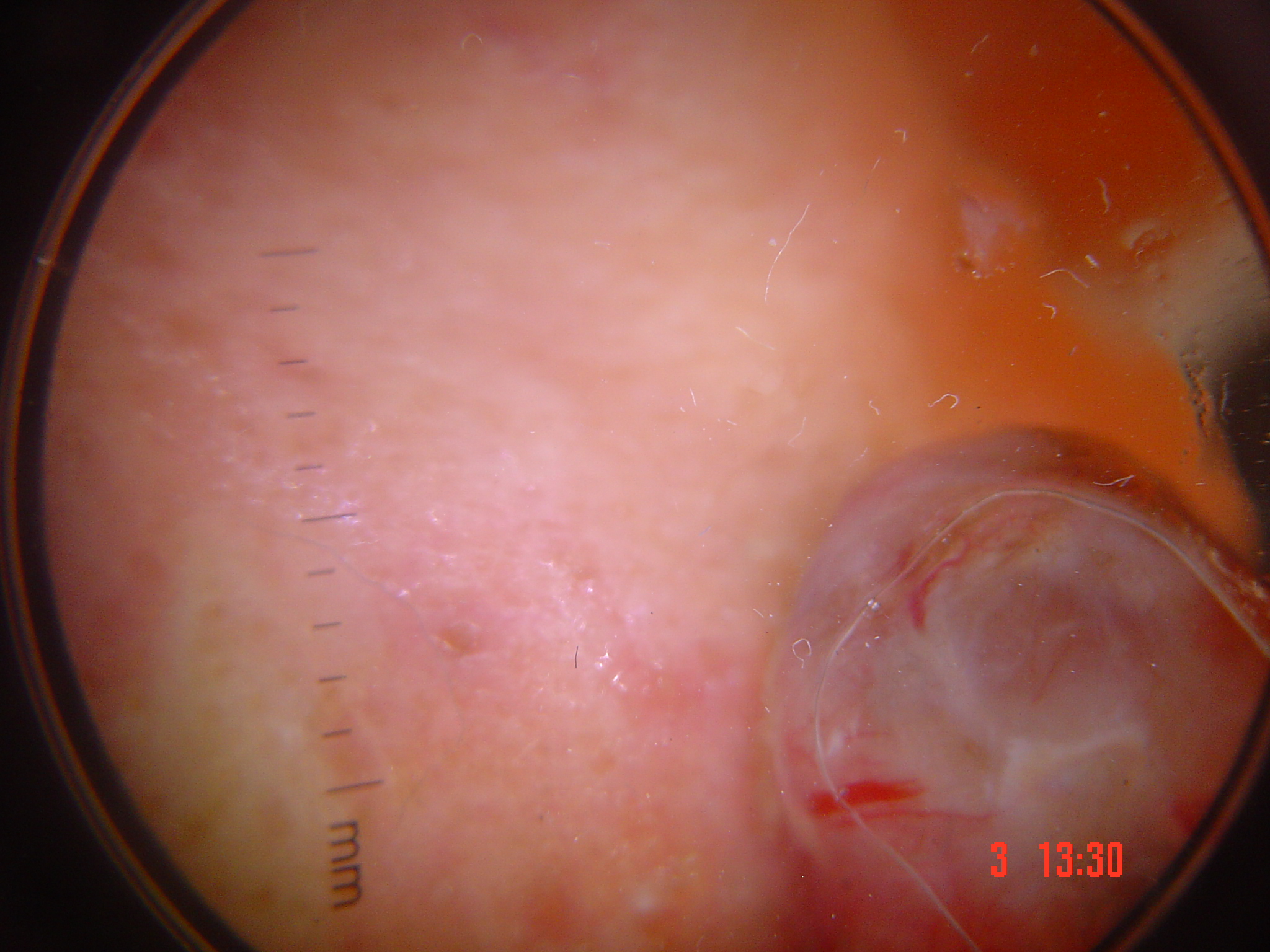Findings: This is a keratinocytic lesion. Conclusion: Histopathology confirmed a malignancy — a basal cell carcinoma.